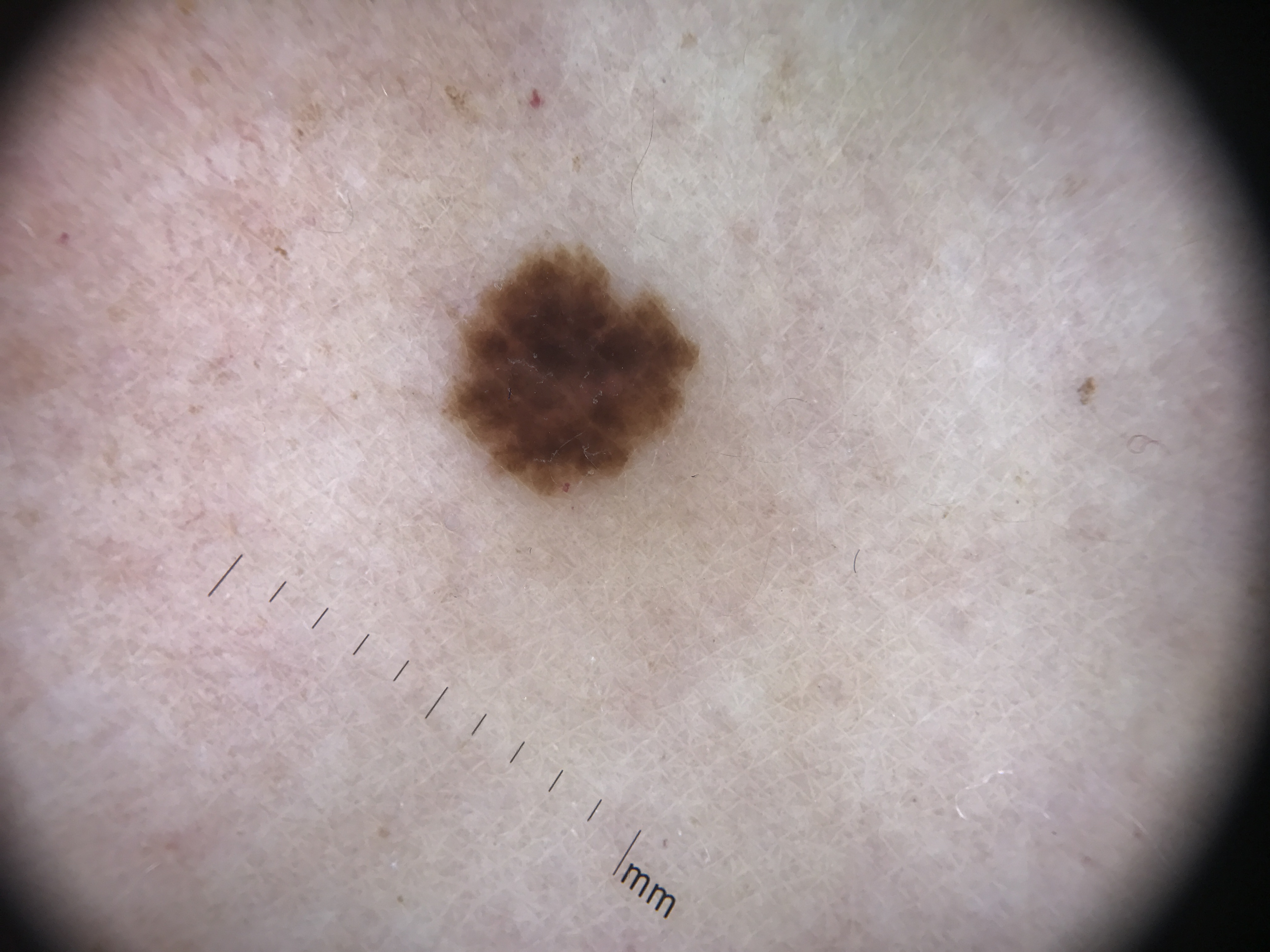A dermoscopic photograph of a skin lesion.
Classified as a dysplastic junctional nevus.